Texture is reported as raised or bumpy. The affected area is the leg, head or neck, back of the hand, palm and arm. The patient described the issue as a rash. Reported lesion symptoms include itching and enlargement. The patient reports the condition has been present for less than one week. An image taken at a distance. Skin tone: Fitzpatrick phototype II; human graders estimated Monk skin tone scale 2. Female contributor, age 40–49.
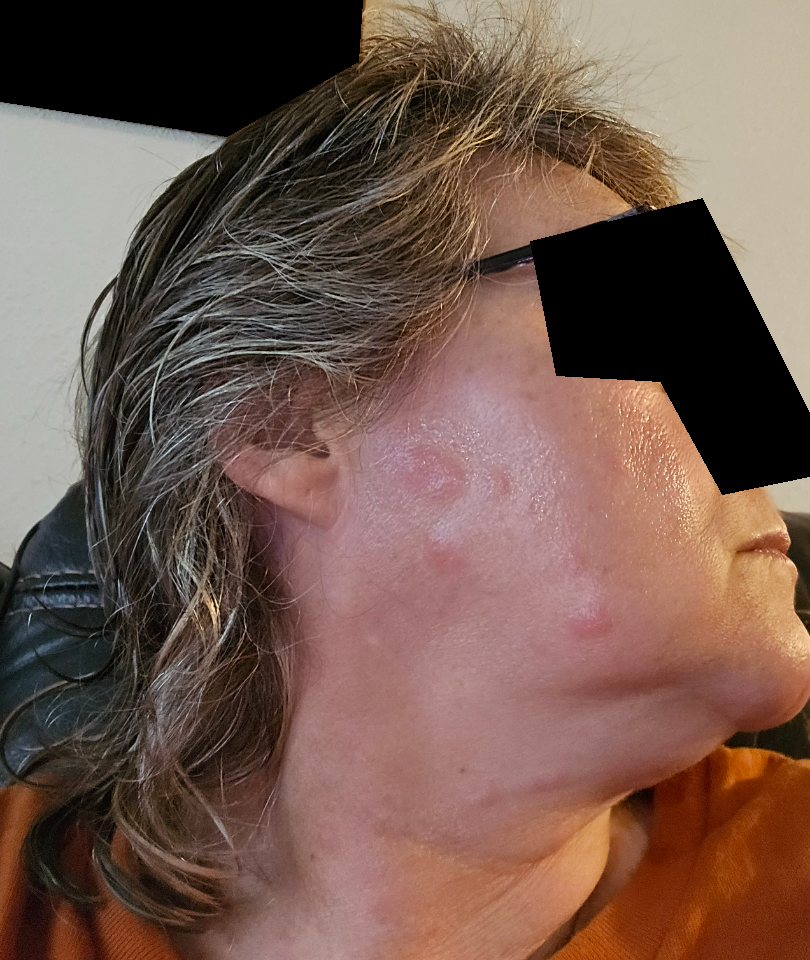Diagnostic features were not clearly distinguishable in this photograph.